Fitzpatrick II, the lesion is described as fluid-filled and raised or bumpy, this is a close-up image: 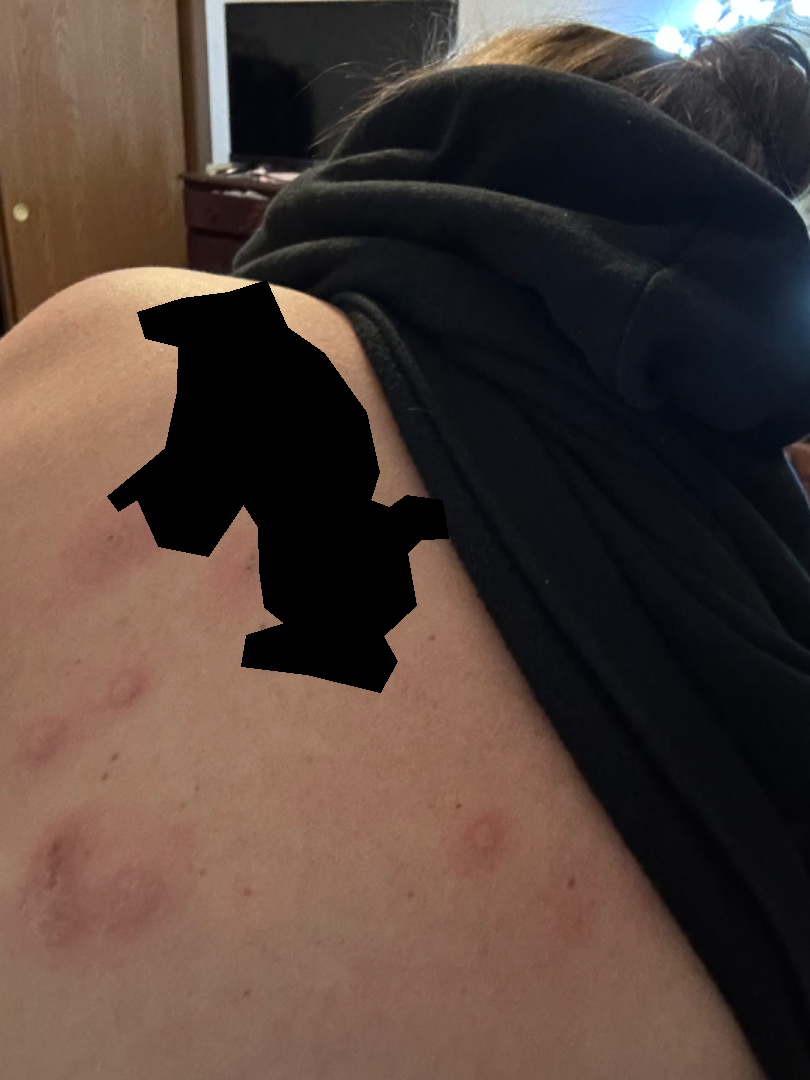Findings: The skin condition could not be confidently assessed from this image.